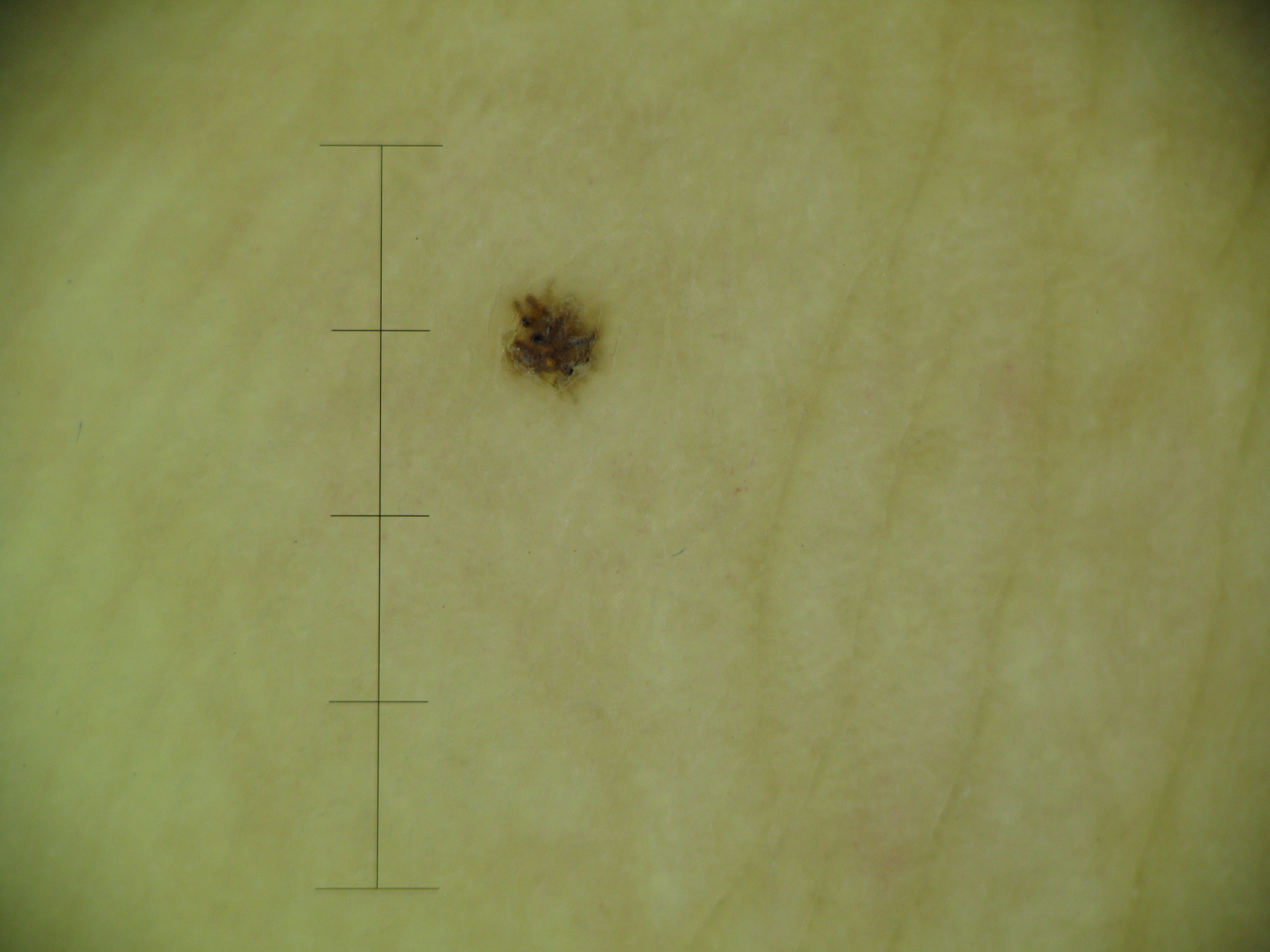assessment=acral dysplastic junctional nevus (expert consensus)